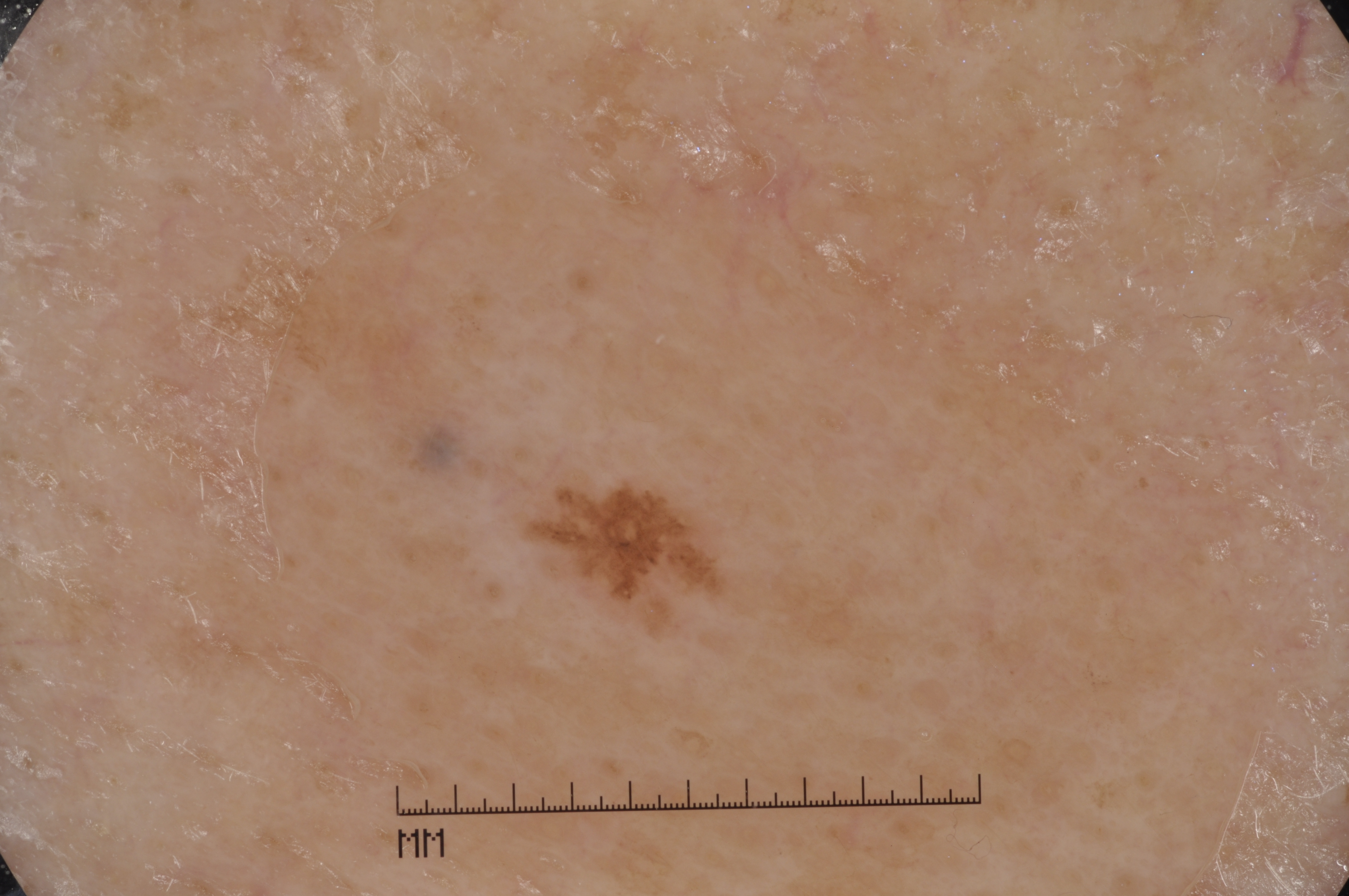Summary:
A dermoscopic view of a skin lesion. A female patient roughly 55 years of age. With coordinates (x1, y1, x2, y2), the lesion is located at 514, 473, 751, 640. Dermoscopy demonstrates no milia-like cysts, streaks, negative network, or pigment network.
Conclusion:
The lesion was assessed as a melanocytic nevus, a benign lesion.